A clinical photograph of a skin lesion. FST II:
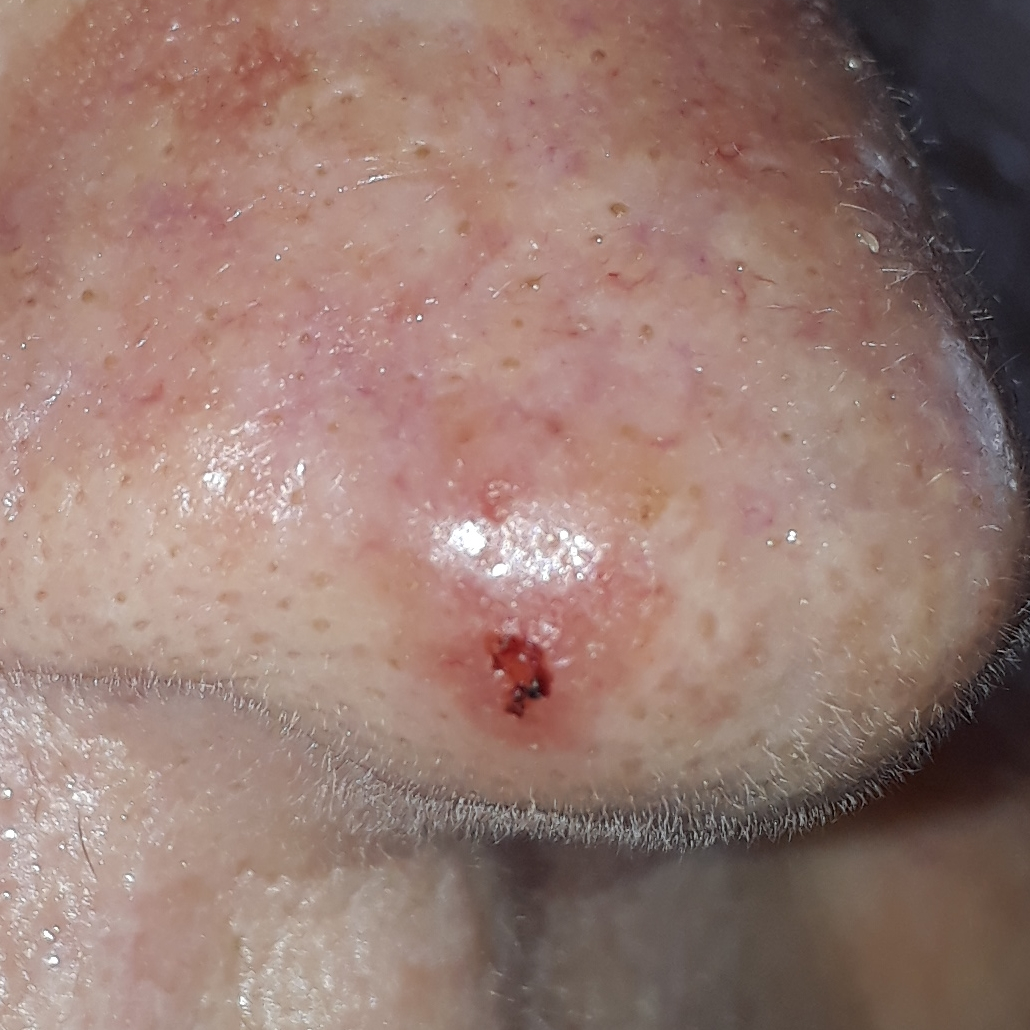region = the nose | patient-reported symptoms = bleeding, itching, elevation | diagnosis = basal cell carcinoma (biopsy-proven).